A contact-polarized dermoscopy image of a skin lesion. A female patient roughly 75 years of age.
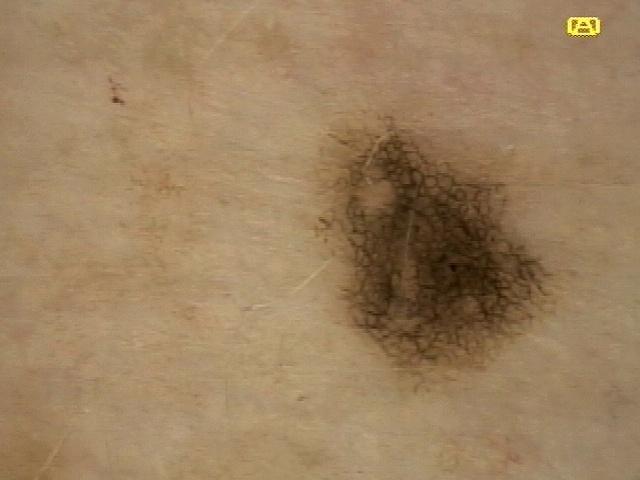Summary:
The lesion involves the trunk.
Conclusion:
The clinical impression was a nevus.